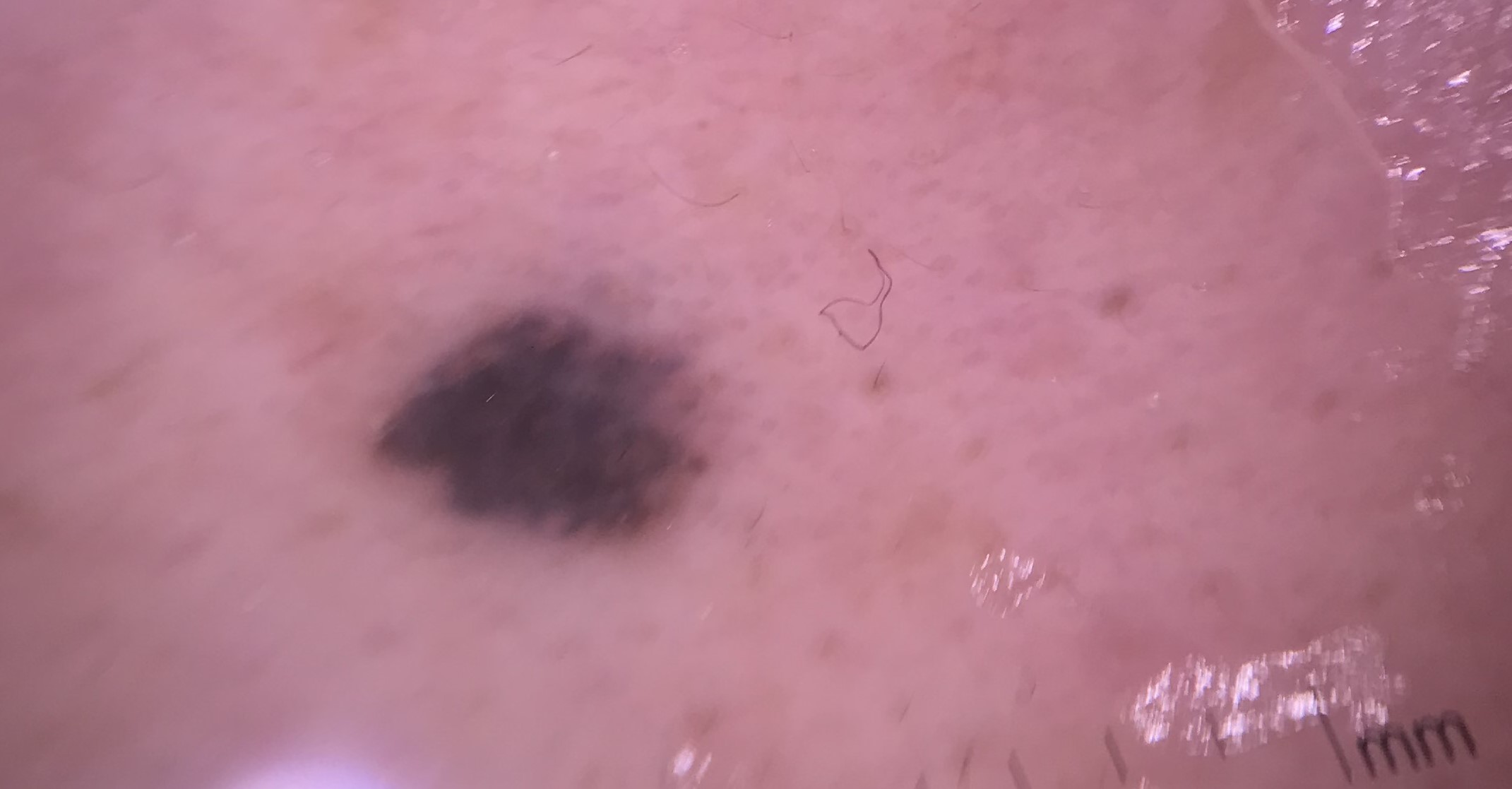imaging: dermatoscopy; category: dermal, banal; class: blue nevus (expert consensus).